A close-up photograph.
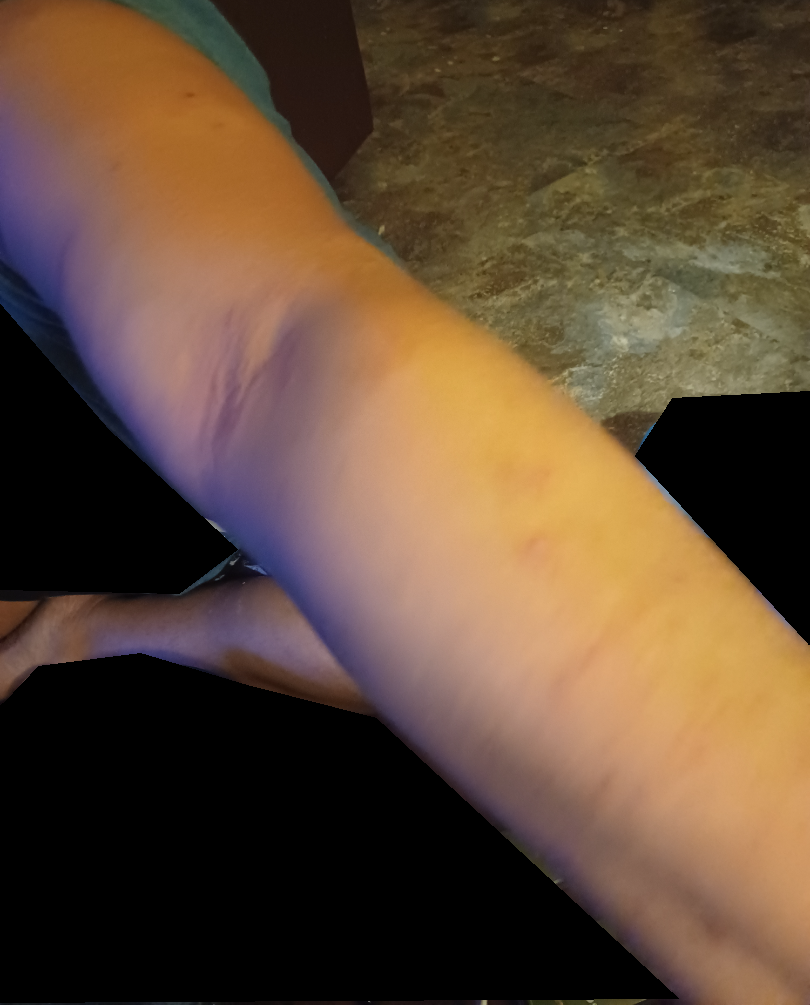Diagnostic features were not clearly distinguishable in this photograph. Skin tone: Fitzpatrick III.